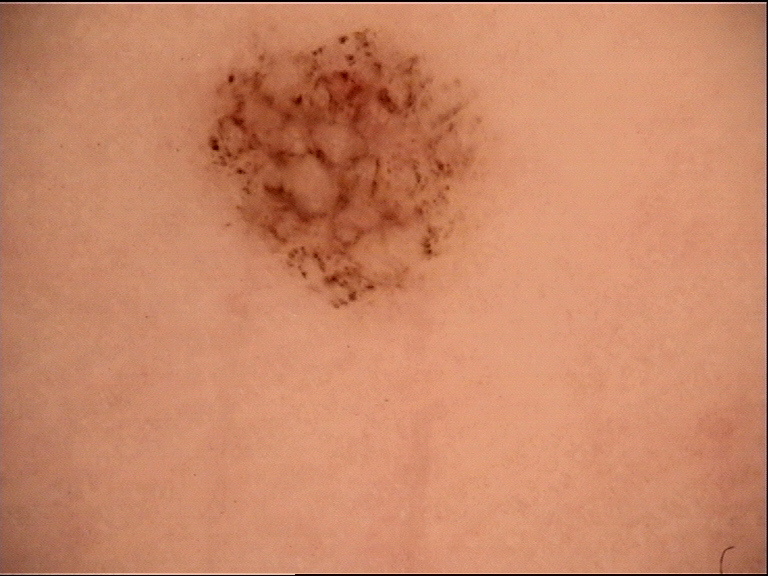A dermoscopic close-up of a skin lesion. The diagnostic label was an acral dysplastic junctional nevus.